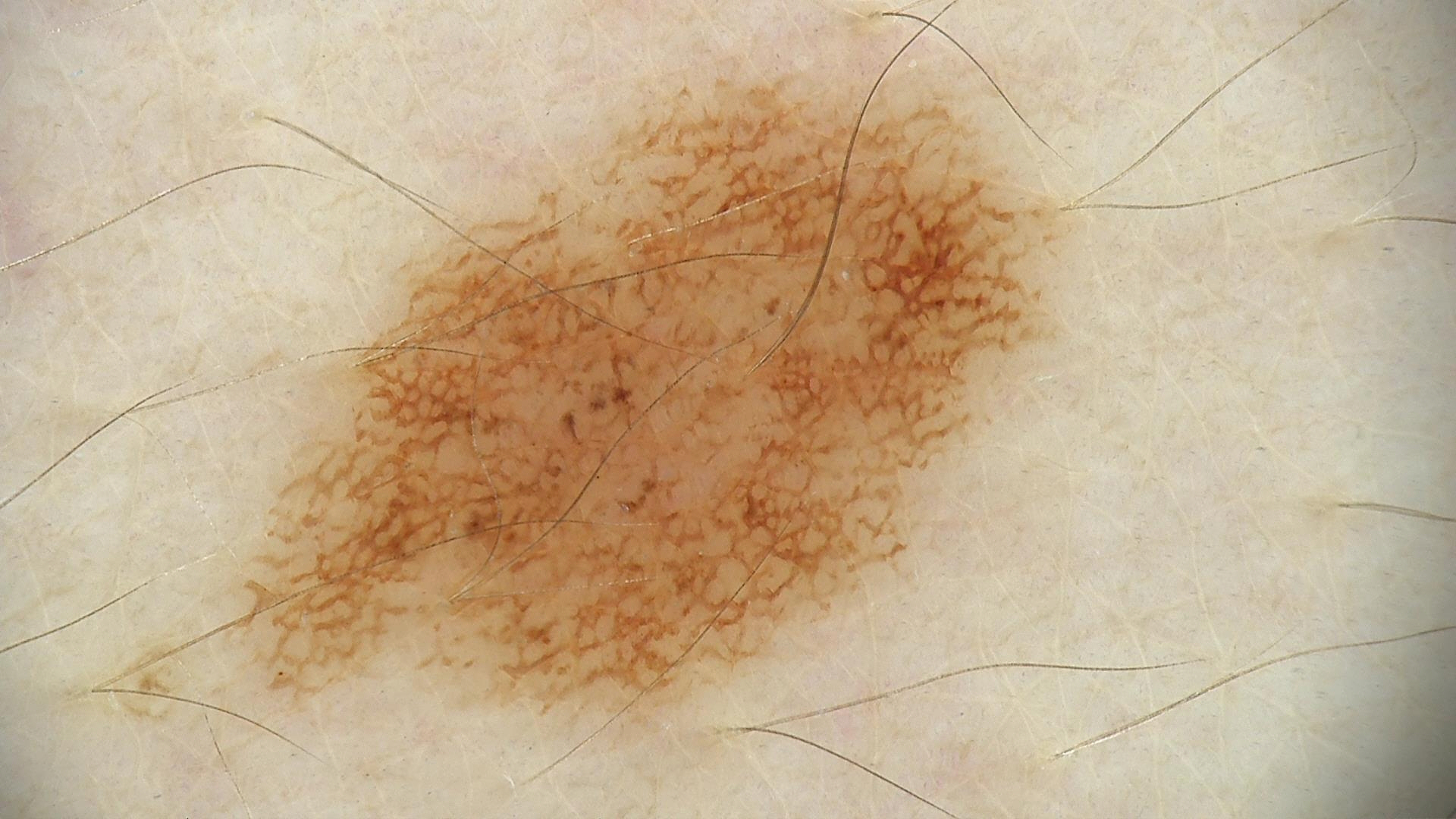Labeled as a dysplastic junctional nevus.